Located on the leg; the contributor is a female aged 40–49; the photograph was taken at a distance.
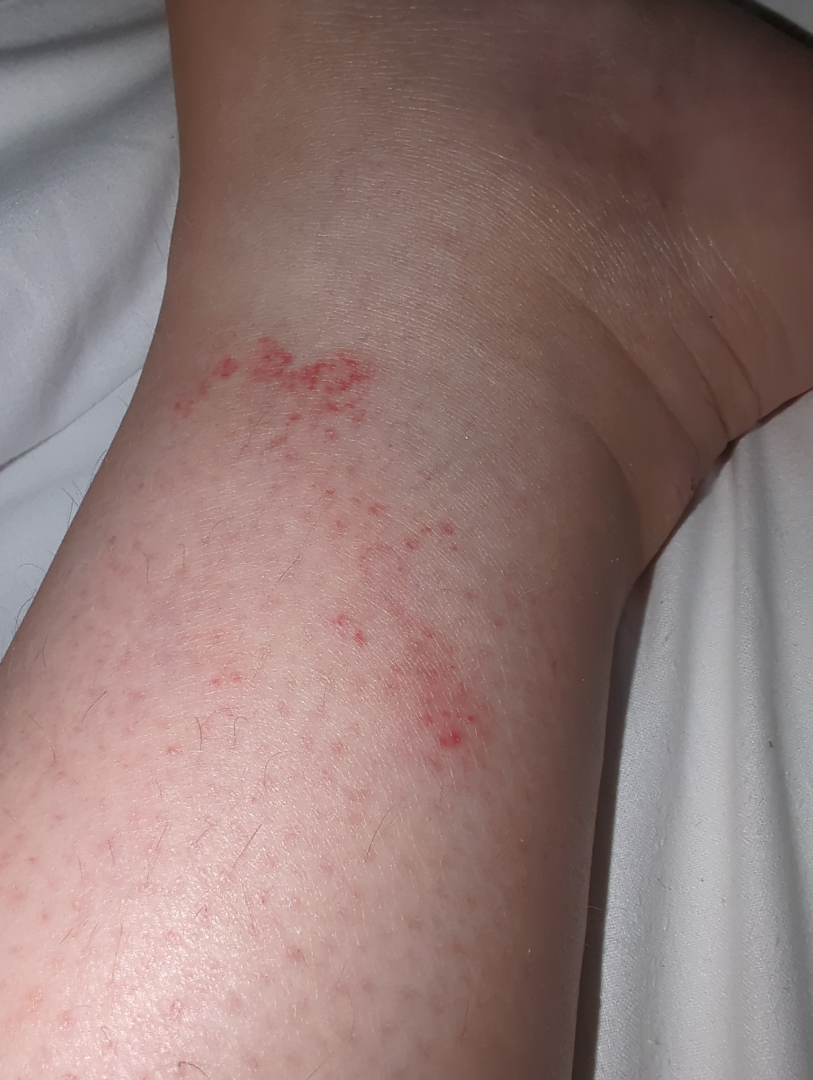On teledermatology review: the differential includes Eczema and Irritant Contact Dermatitis, with no clear leading consideration.